The patient describes having few moles overall; on a questionnaire the patient reported no personal history of skin cancer; a male subject 15 years of age; the patient says their skin tans without first burning; a skin lesion imaged with a dermatoscope; referred for assessment of suspected melanocytic nevus.
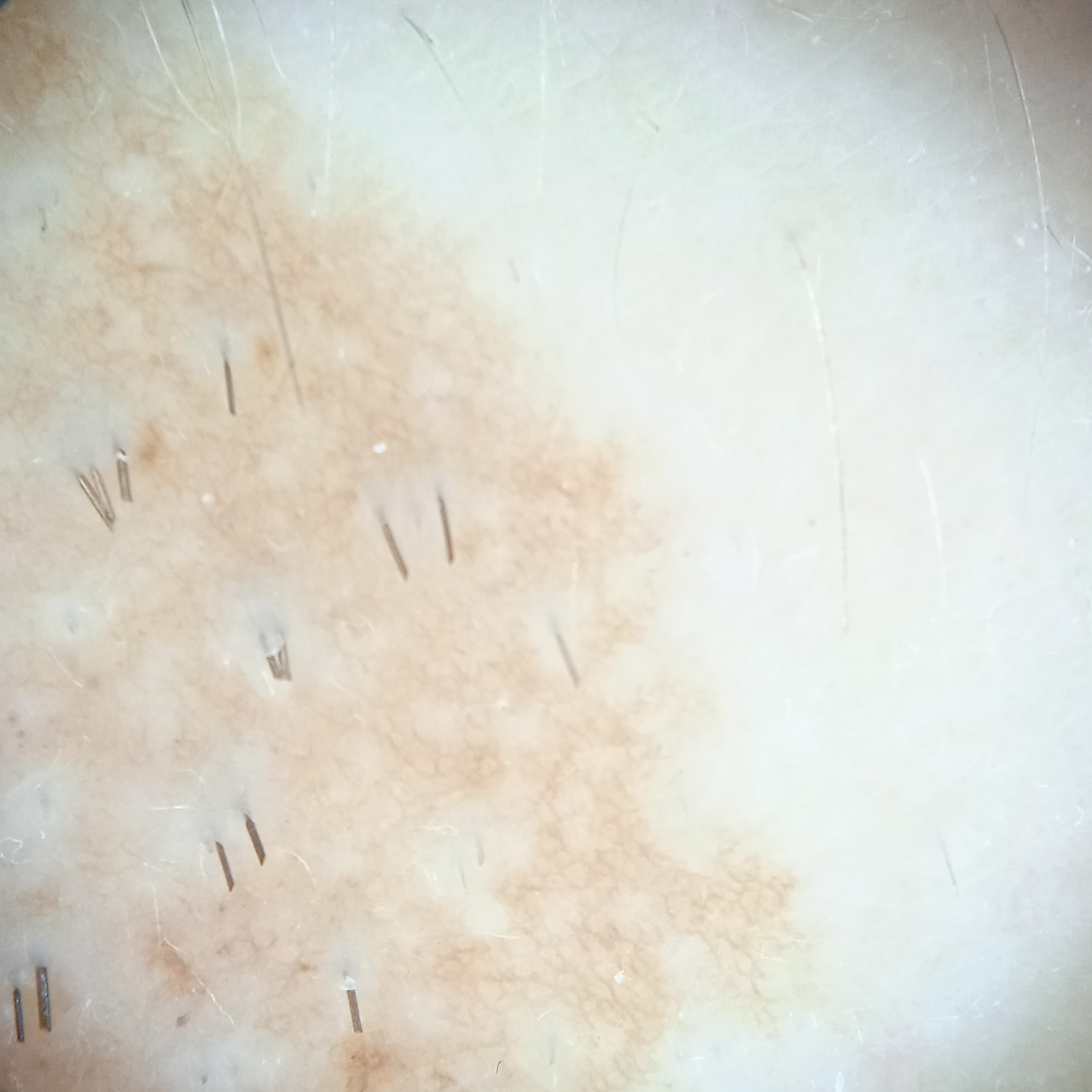<case>
<lesion_location>an arm</lesion_location>
<lesion_size>
<diameter_mm>26.1</diameter_mm>
</lesion_size>
<diagnosis>
<name>melanocytic nevus</name>
<malignancy>benign</malignancy>
<procedure>punch biopsy</procedure>
</diagnosis>
</case>